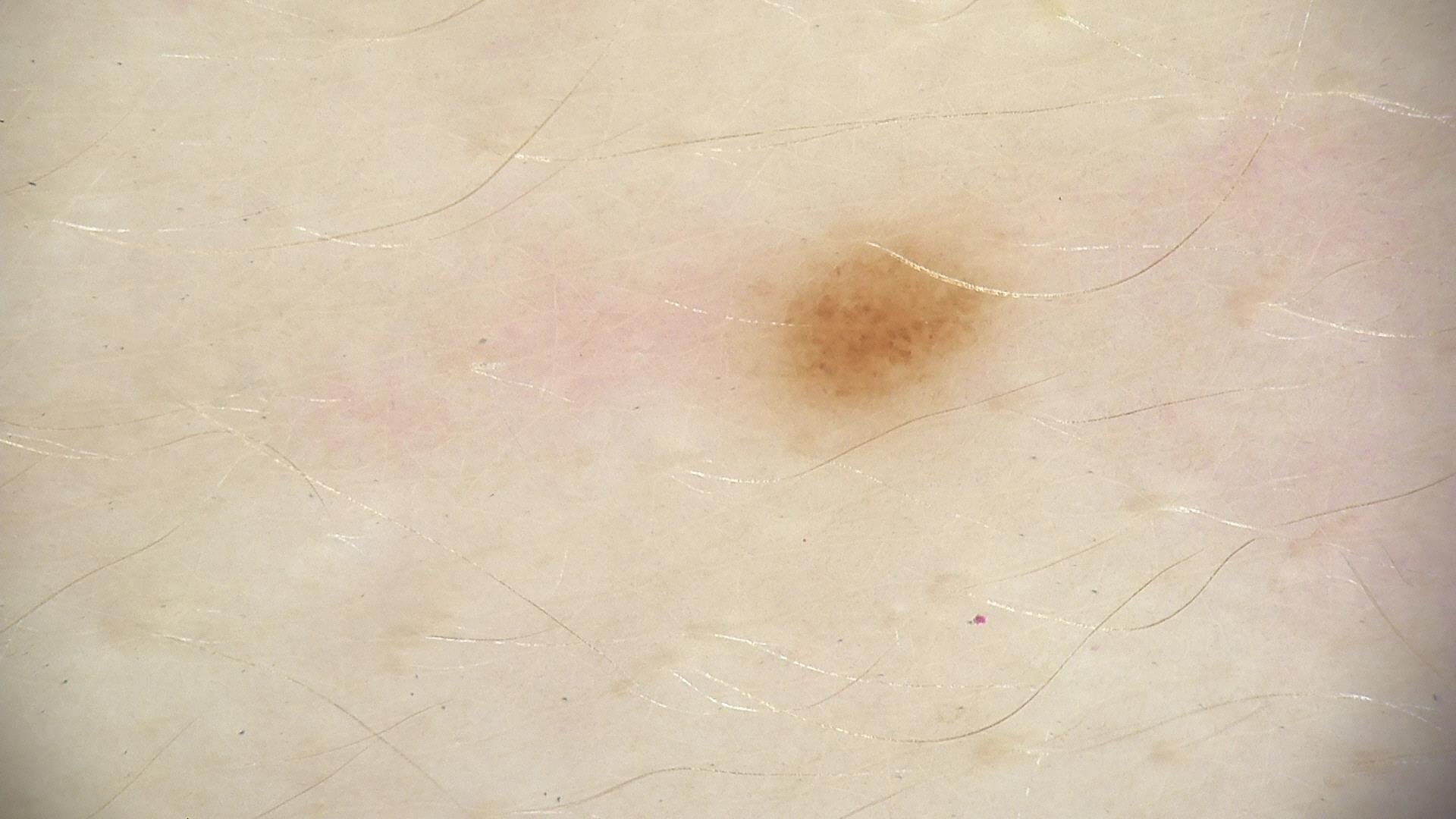• image · dermoscopy
• diagnostic label · dysplastic junctional nevus (expert consensus)